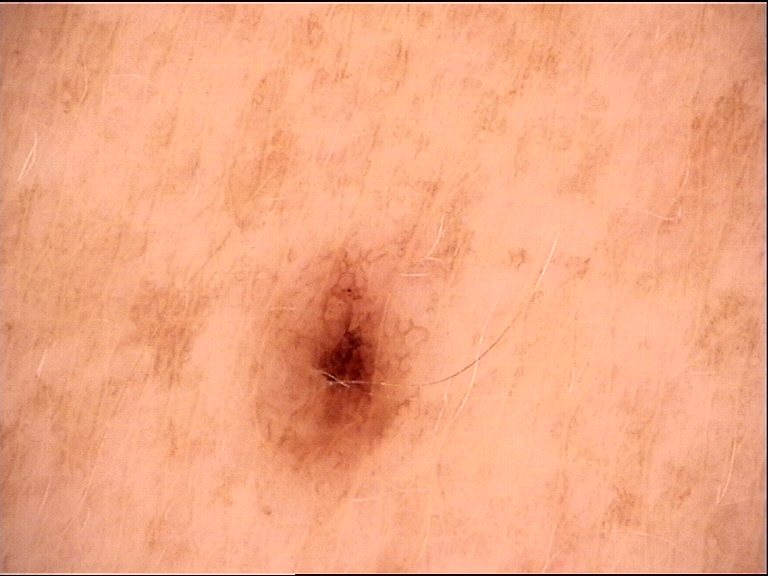| key | value |
|---|---|
| image | dermatoscopy |
| label | dysplastic junctional nevus (expert consensus) |